A dermoscopic close-up of a skin lesion:
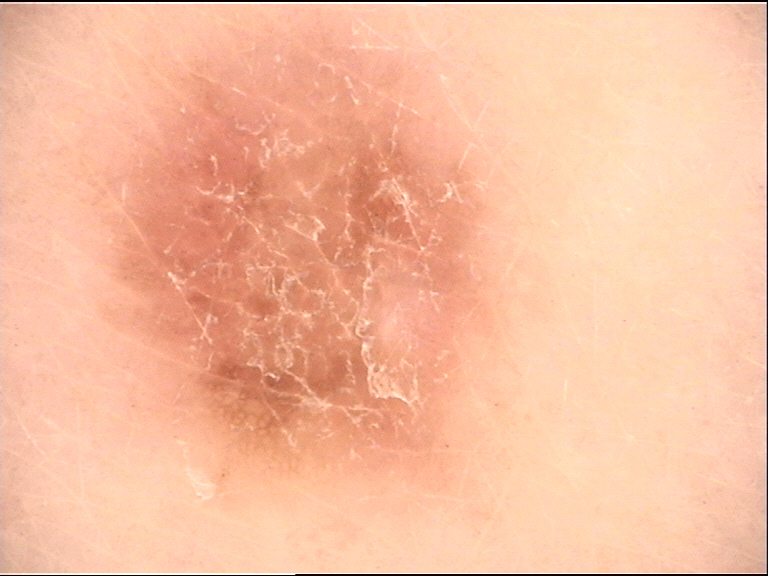lesion type = banal
class = junctional nevus (expert consensus)